The condition has been present for less than one week · self-categorized by the patient as a rash · the photo was captured at an angle · the contributor reports the lesion is raised or bumpy and fluid-filled · the arm and back of the torso are involved · the subject is 50–59, female · the contributor reports itching:
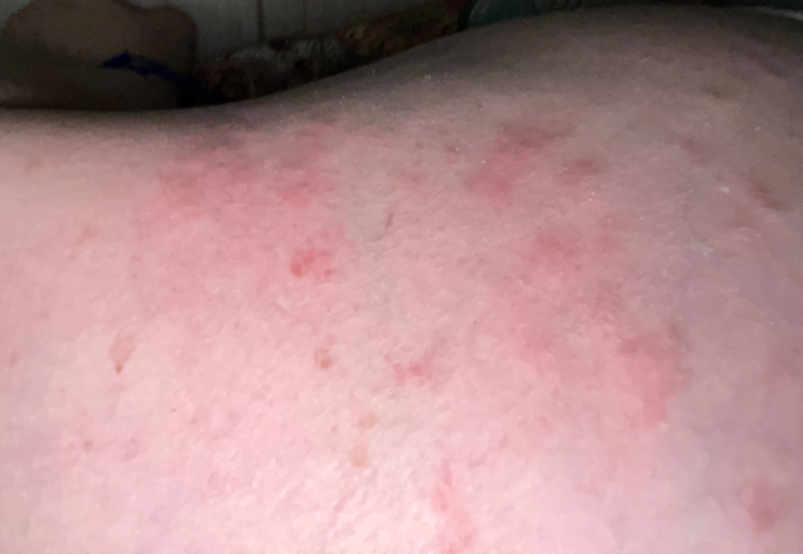The reviewing dermatologist was unable to assign a differential diagnosis from the image.